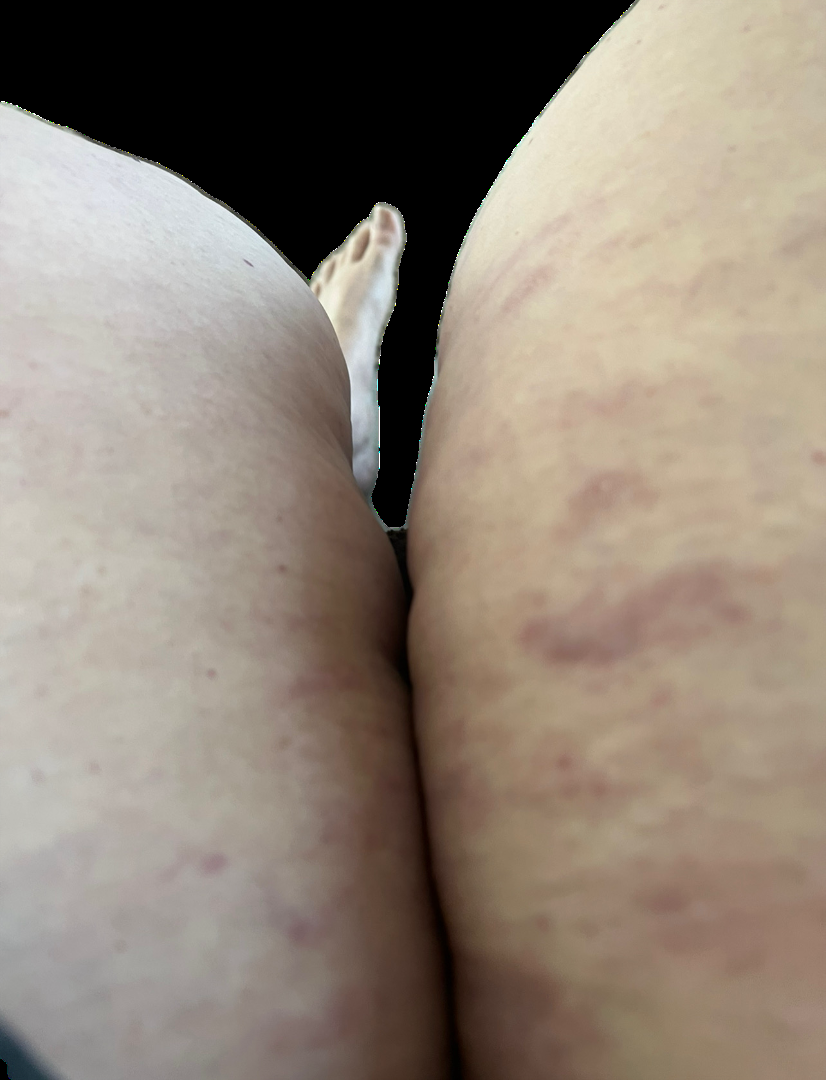The affected area is the arm and leg. Texture is reported as raised or bumpy, flat and rough or flaky. The patient reports associated joint pain and fatigue. The patient reports the condition has been present for one to four weeks. Non-clinician graders estimated 2 on the Monk Skin Tone. An image taken at a distance. The patient considered this skin that appeared healthy to them. One reviewing dermatologist: Cutaneous T Cell Lymphoma, Granuloma annulare and Eczema were considered with similar weight.